A dermoscopy image of a single skin lesion.
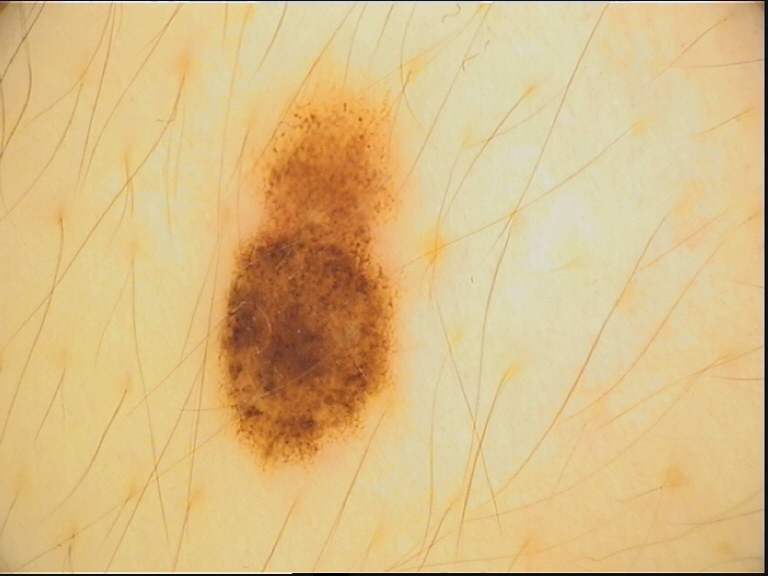Q: What is this lesion?
A: dysplastic compound nevus (expert consensus)